Self-categorized by the patient as a rash; reported lesion symptoms include bothersome appearance, itching and burning; the photograph was taken at an angle; the contributor is 40–49, female; the patient indicates the lesion is raised or bumpy and fluid-filled; located on the back of the hand and arm.
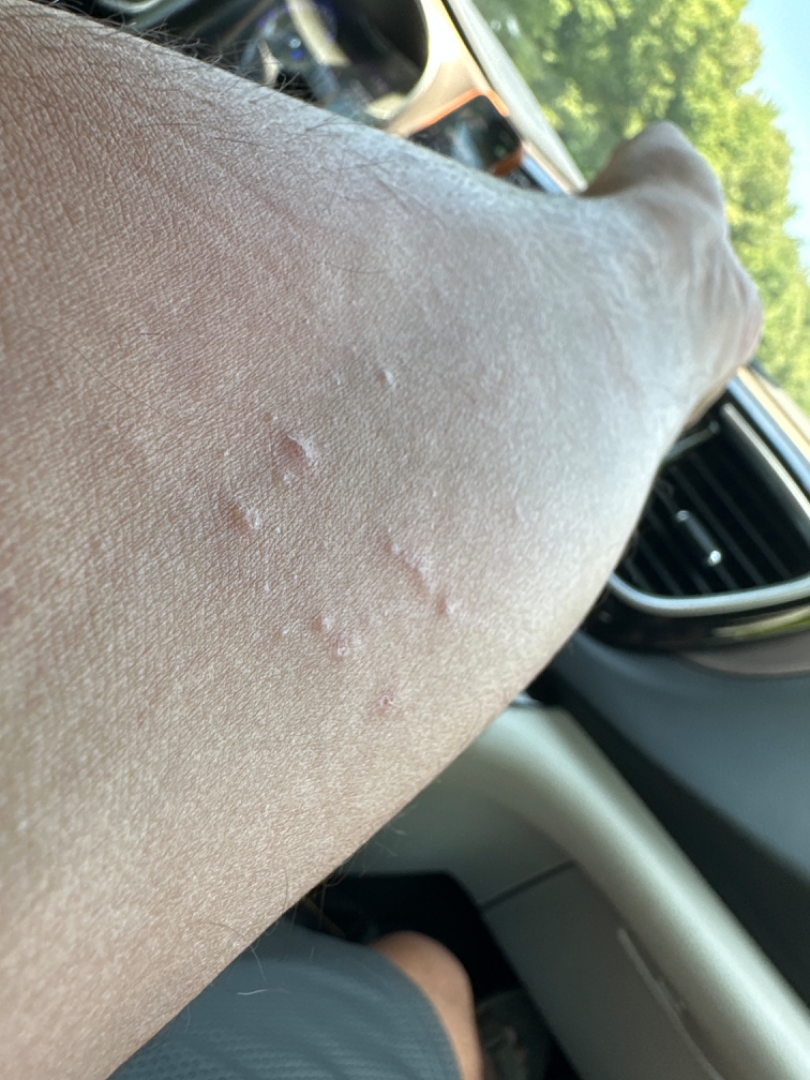* clinical impression · the leading consideration is Molluscum Contagiosum; also on the differential is Insect Bite; possibly Allergic Contact Dermatitis